A dermoscopic photograph of a skin lesion.
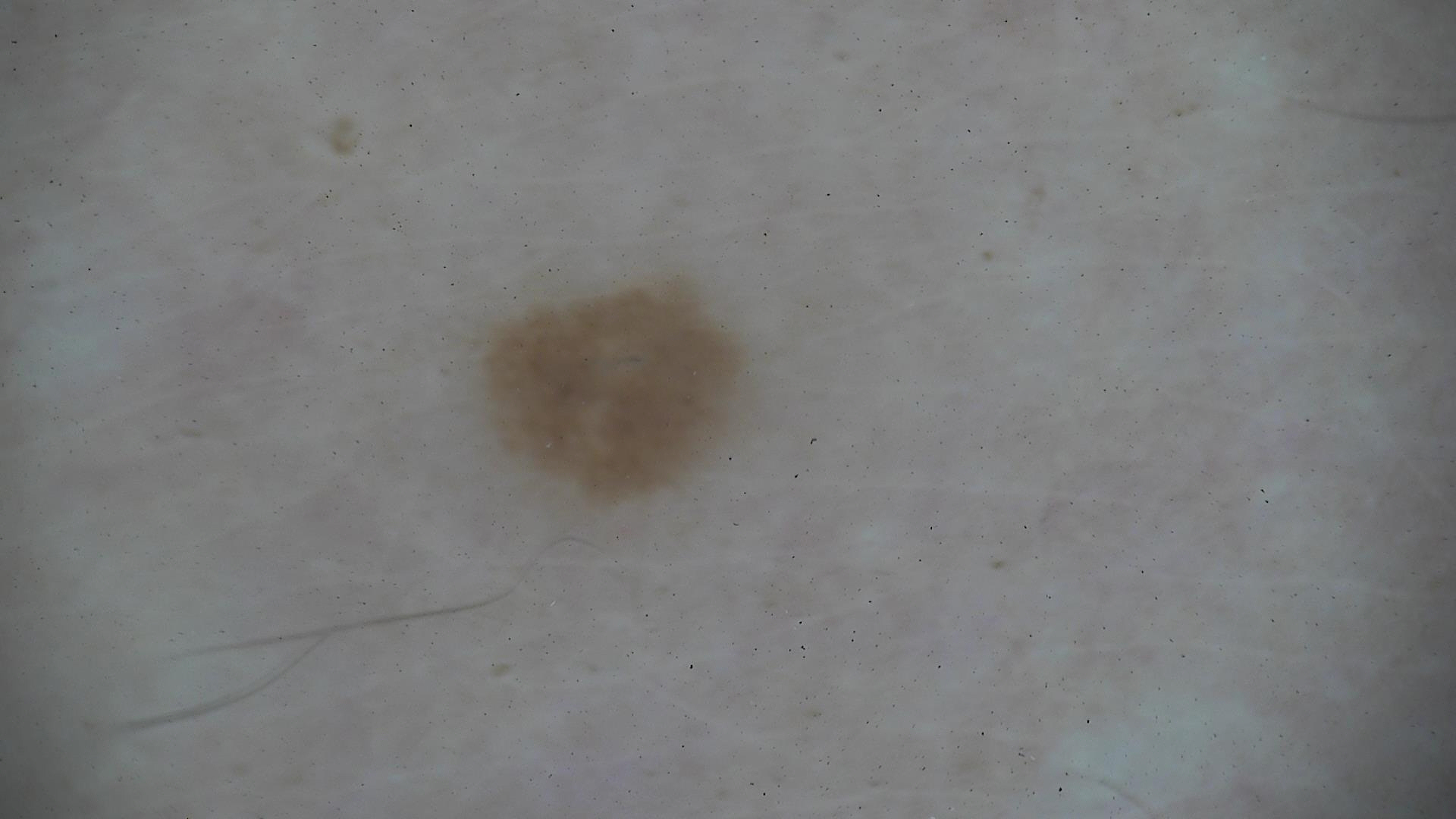label = dysplastic junctional nevus (expert consensus).